The photo was captured at a distance.
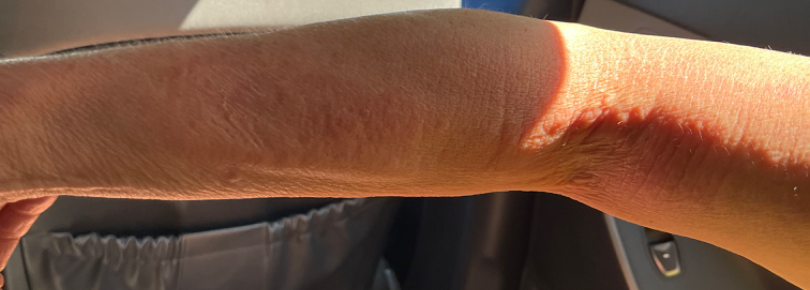| key | value |
|---|---|
| assessment | ungradable on photographic review |